A male patient aged 58 — 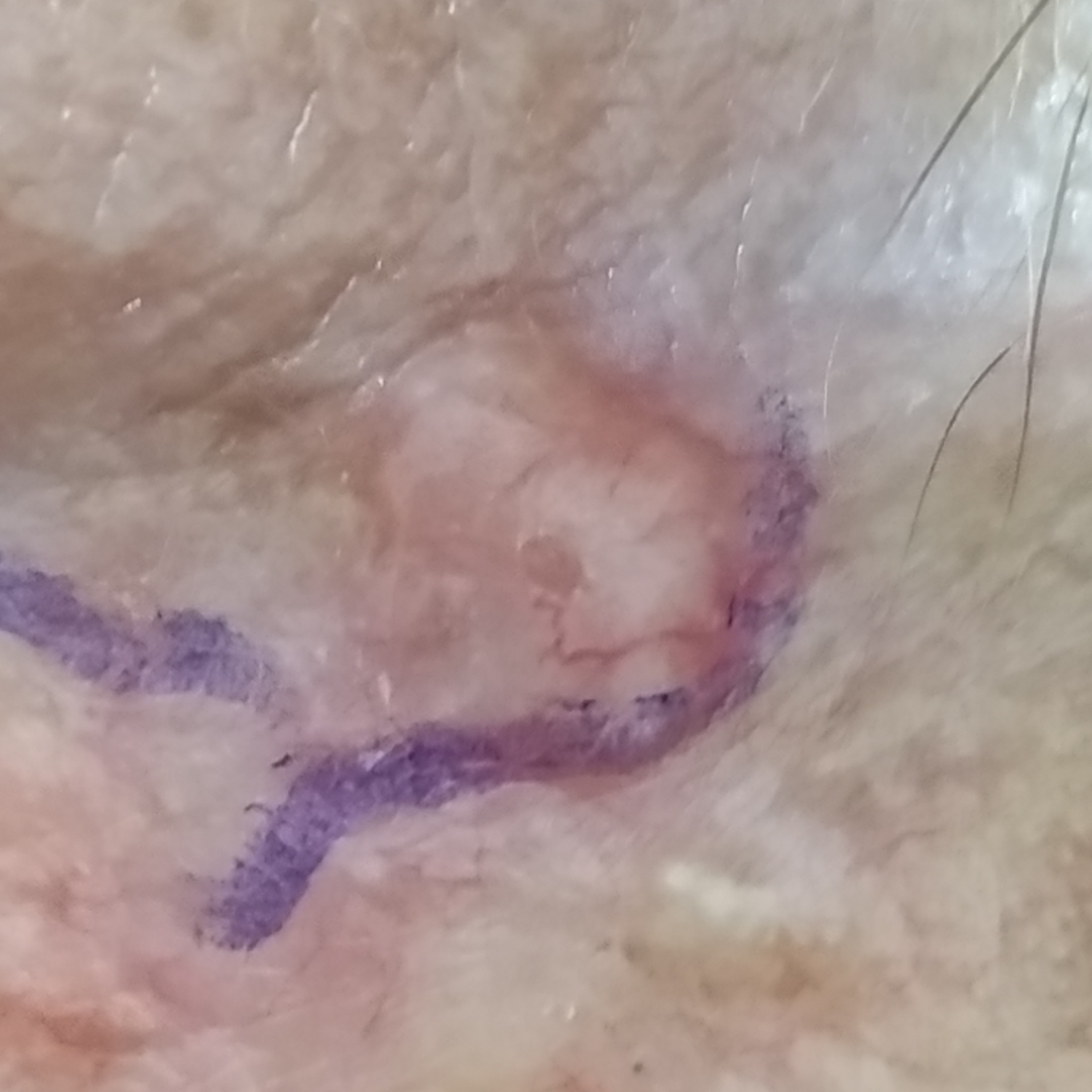The lesion is located on the face. Histopathological examination showed a basal cell carcinoma.